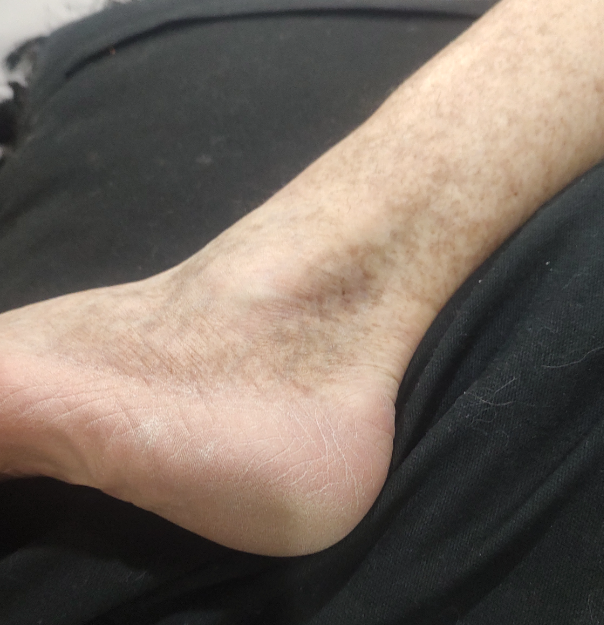The patient considered this a pigmentary problem. No relevant systemic symptoms. An image taken at an angle. The condition has been present for one to three months. The lesion involves the top or side of the foot. Female patient, age 50–59. Texture is reported as flat. The patient reports bothersome appearance. On photographic review by a dermatologist, the reviewer's impression was Hemosiderin pigmentation of skin due to venous insufficiency.